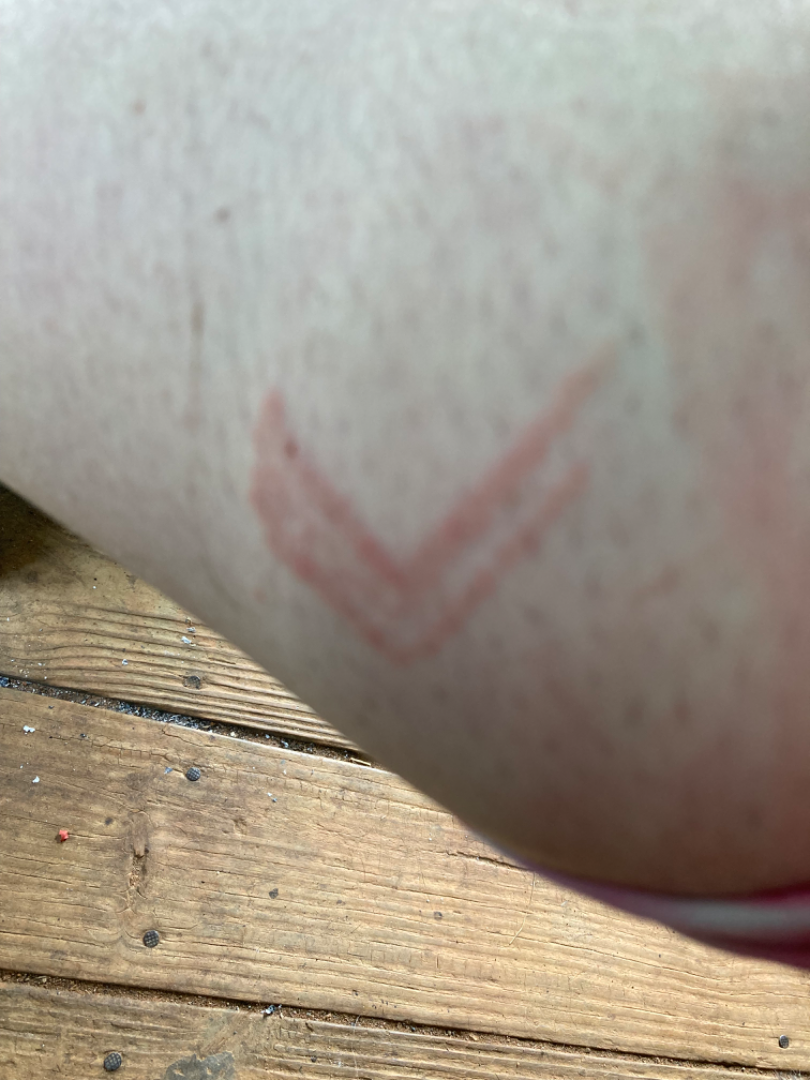Q: What is the dermatologist's impression?
A: Burn of skin (considered); Allergic Contact Dermatitis (considered)